The photograph was taken at an angle. The affected area is the leg. The patient is 40–49, female — 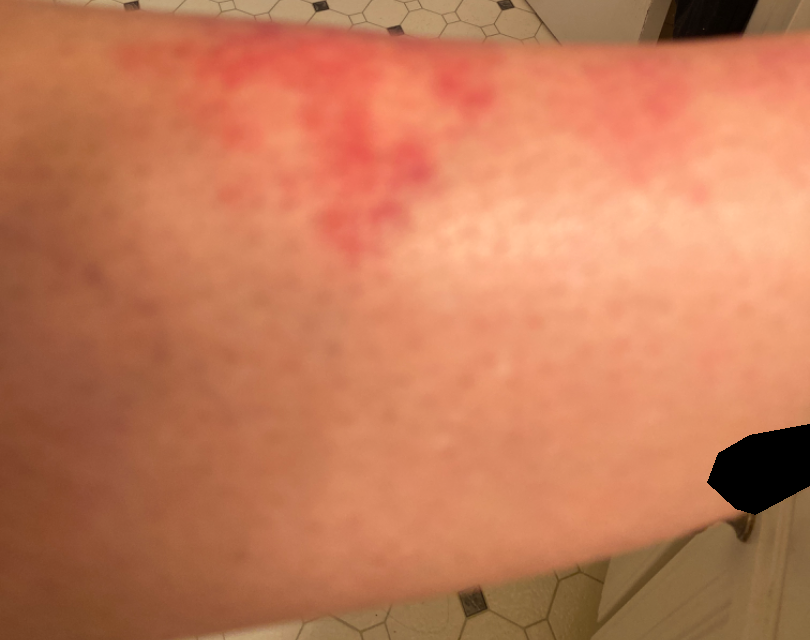No associated lesion symptoms were reported.
The patient reports the condition has been present for about one day.
The patient reports the lesion is flat.
Single-reviewer assessment: most consistent with Acute dermatitis, NOS.